The condition has been present for about one day, the patient described the issue as a rash, reported lesion symptoms include itching, the lesion is described as raised or bumpy, no constitutional symptoms were reported, the affected area is the arm, the patient is a male aged 30–39, the photograph was taken at an angle: 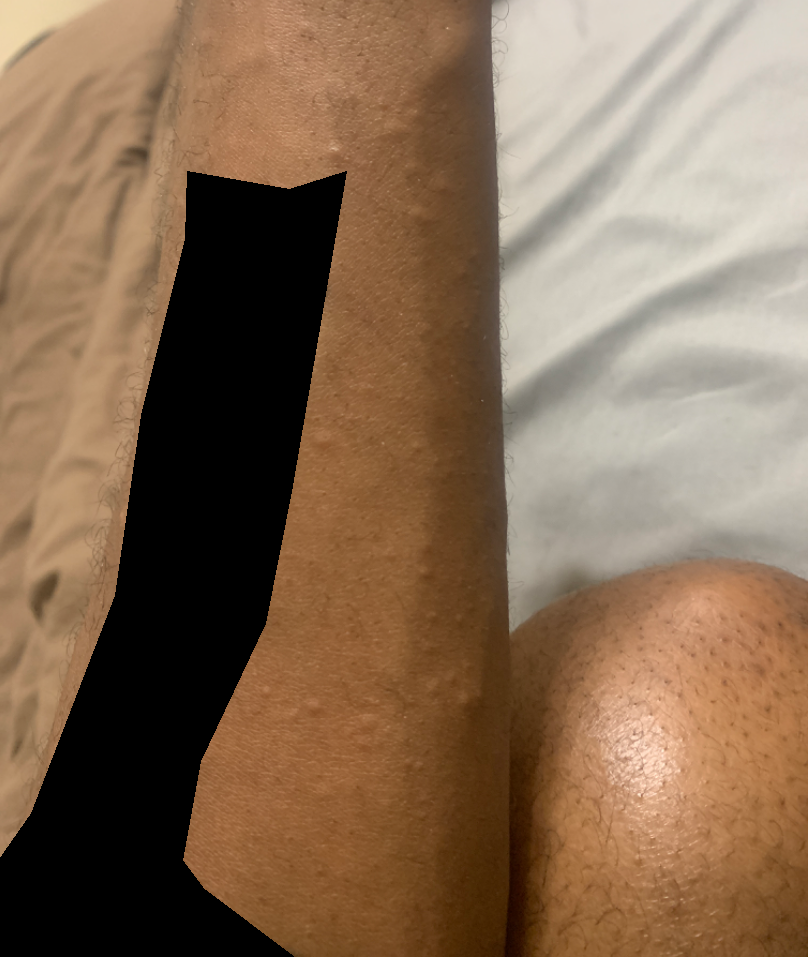Impression:
On photographic review: Lichenoid myxedema (primary); Clinical neurofibromatosis (possible).